A male patient 72 years old; a dermoscopy image of a skin lesion; the patient says their skin reddens with sun exposure; few moles overall by the patient's own estimate — 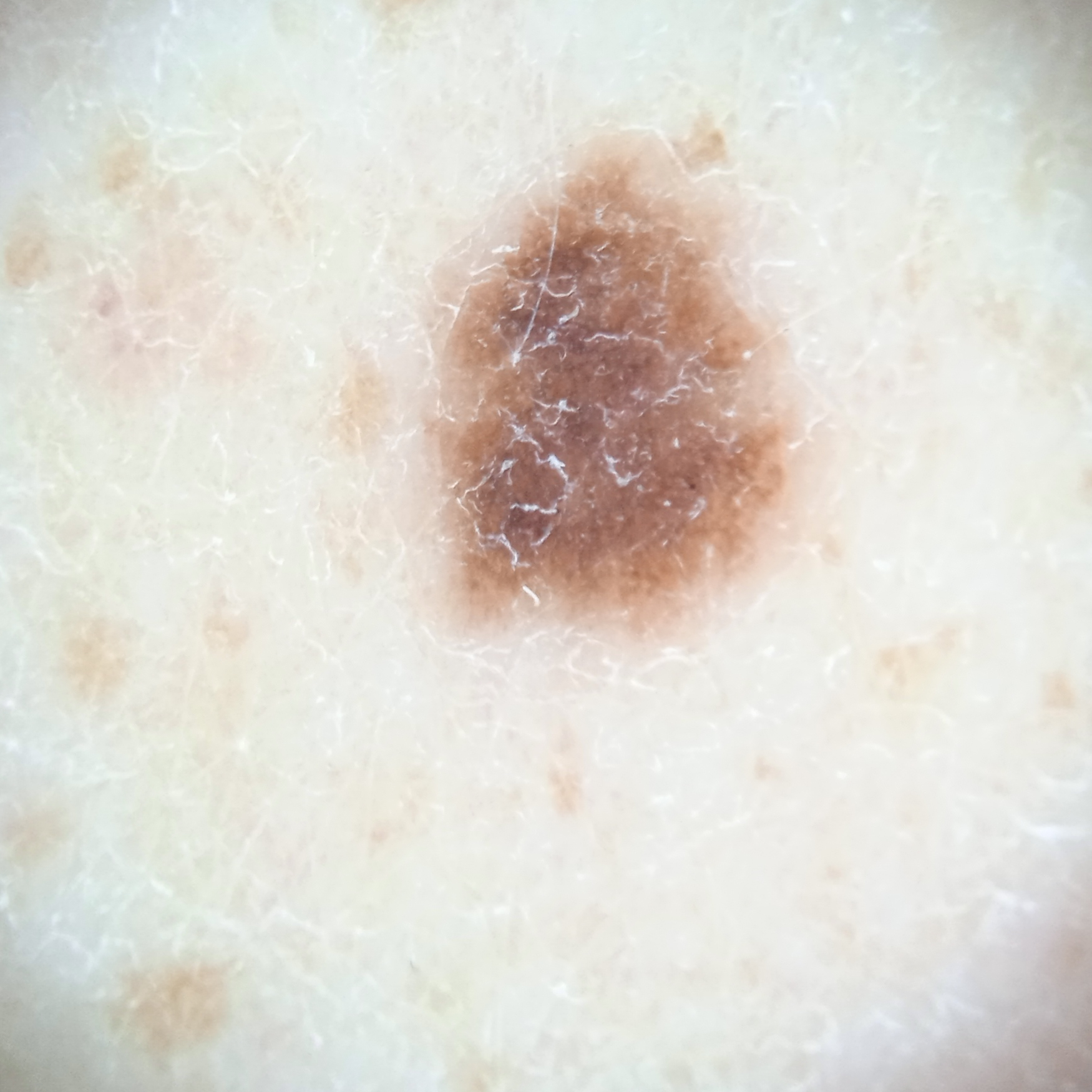Q: Where is the lesion?
A: the back
Q: What was the diagnosis?
A: melanocytic nevus (dermatologist consensus)